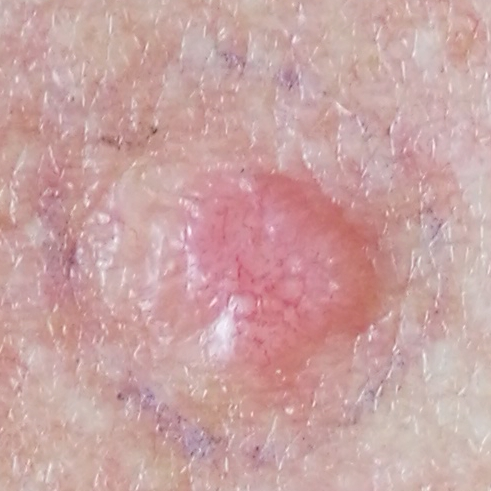A female subject age 54. A clinical photograph of a skin lesion. Recorded as Fitzpatrick II. By history, prior malignancy (patient or family). The lesion involves the back. The lesion measures approximately 7 × 6 mm. Per patient report, the lesion has grown, itches, is elevated, and has bled. On biopsy, the diagnosis was a basal cell carcinoma.